A dermoscopic image of a skin lesion.
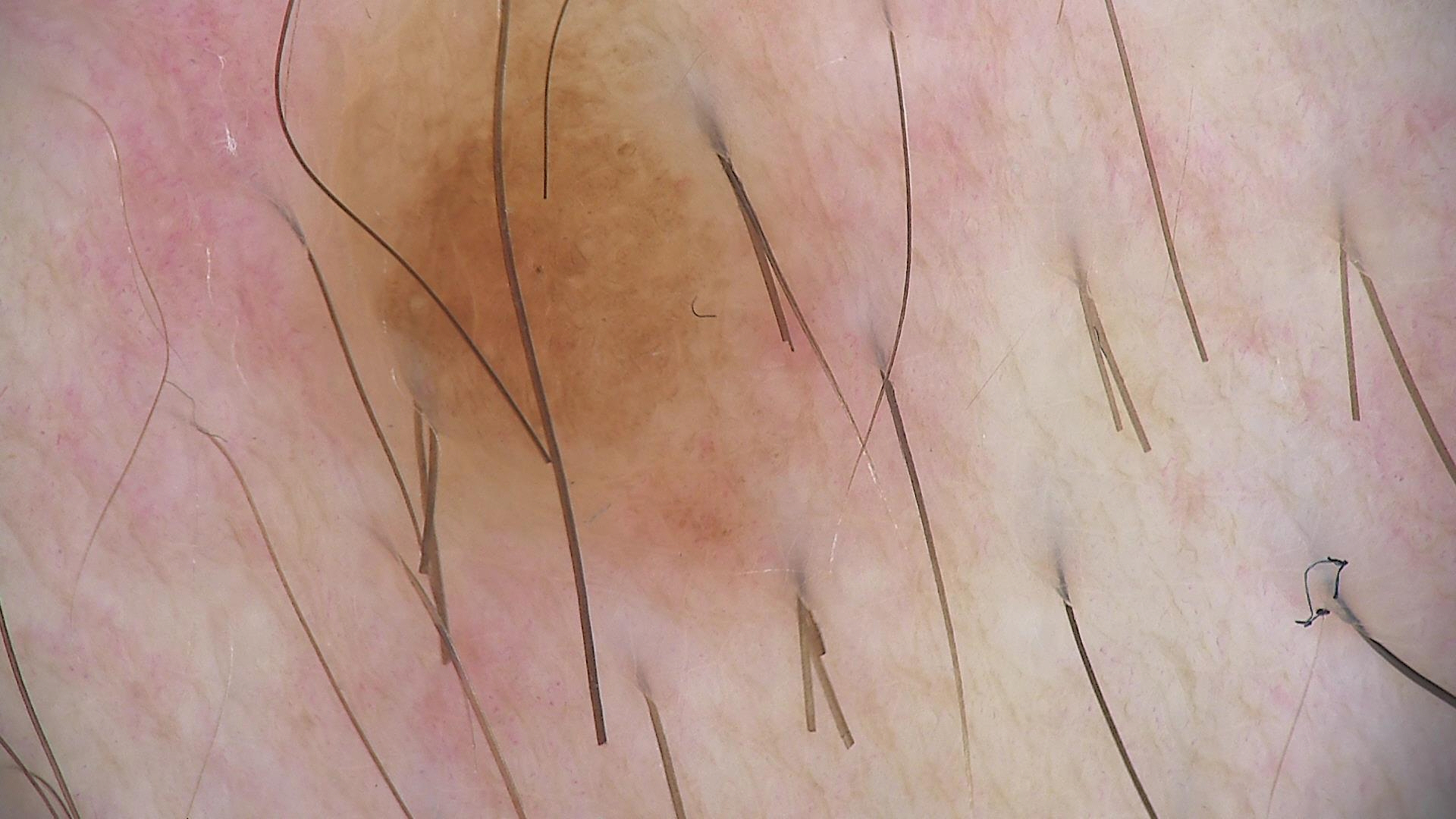Findings: The architecture is that of a banal lesion. Impression: The diagnosis was a dermal nevus.